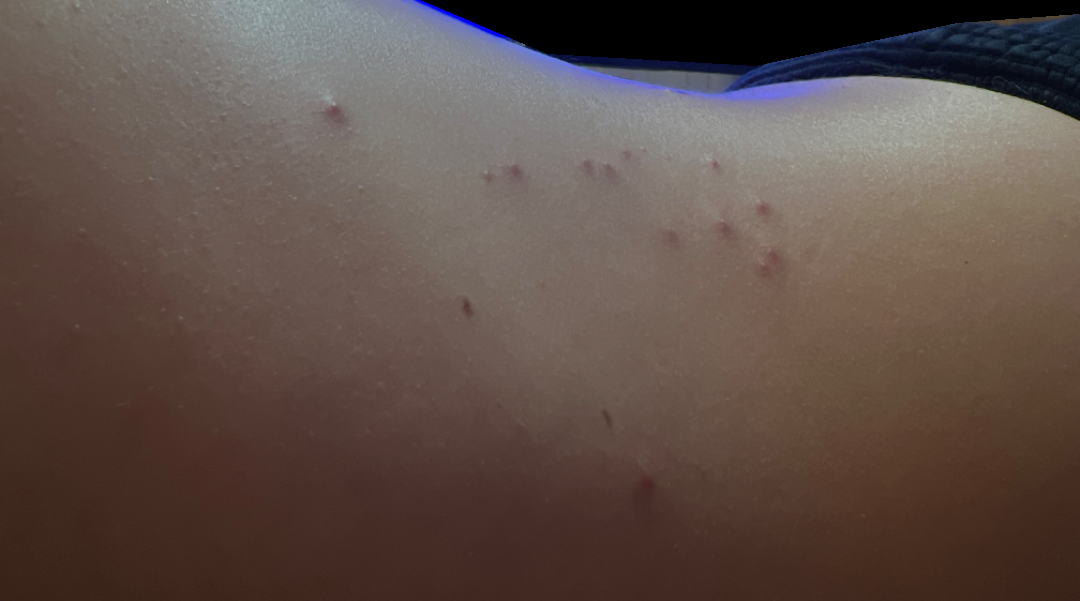Review:
The image was not sufficient for the reviewer to characterize the skin condition.
Patient information:
Located on the back of the torso and arm. Reported lesion symptoms include itching. The photo was captured at an angle. Present for less than one week. Non-clinician graders estimated MST 2 (US pool) or 3 (India pool).